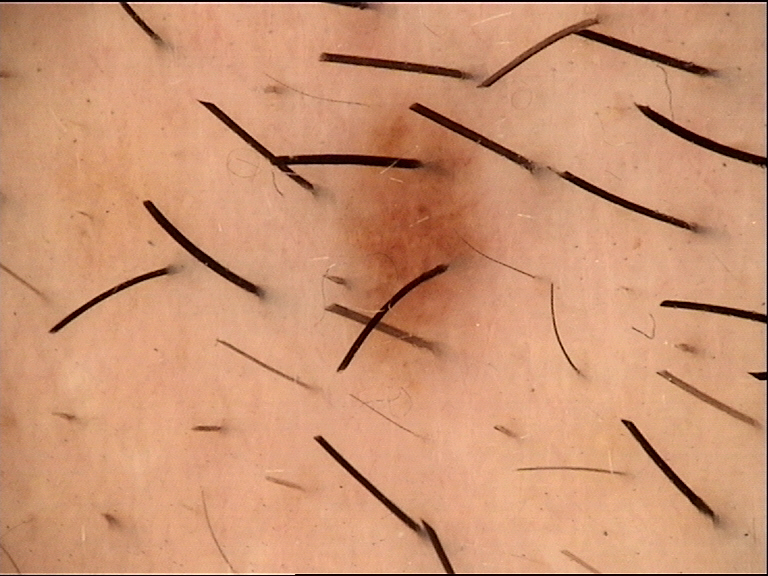A dermoscopic close-up of a skin lesion. Labeled as a benign lesion — a dysplastic junctional nevus.